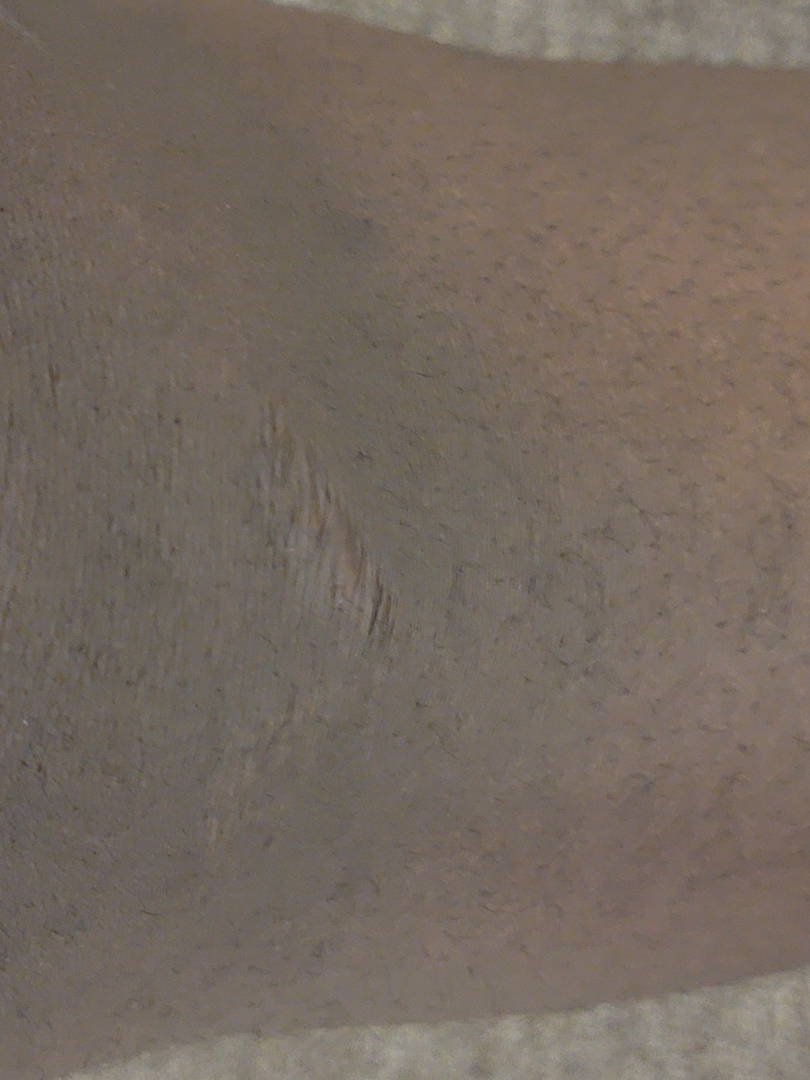{
  "patient": "male, age 30–39",
  "symptoms": "darkening",
  "shot_type": "at an angle",
  "texture": "raised or bumpy",
  "body_site": "leg",
  "differential": {
    "leading": [
      "Scar Condition"
    ],
    "considered": [
      "Anetoderma"
    ]
  }
}